A dermoscopic view of a skin lesion, a male subject approximately 60 years of age:
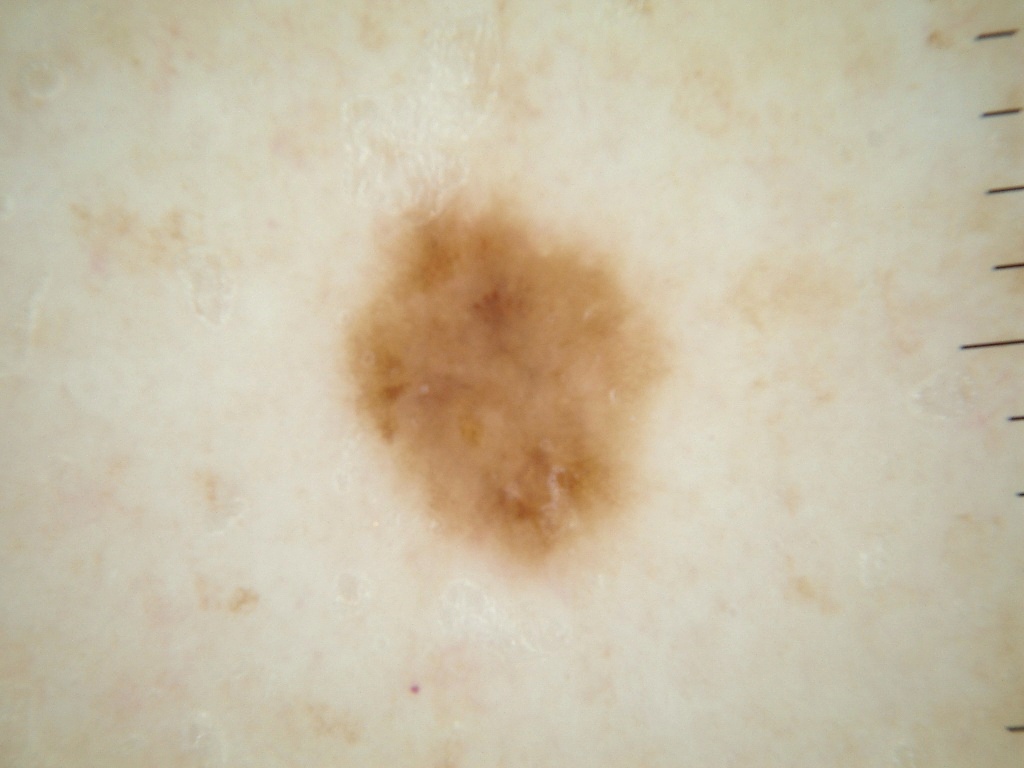The lesion's extent is bbox=[338, 184, 670, 577]. Dermoscopically, the lesion shows pigment network, with no globules, streaks, milia-like cysts, or negative network. The diagnostic assessment was a melanocytic nevus.